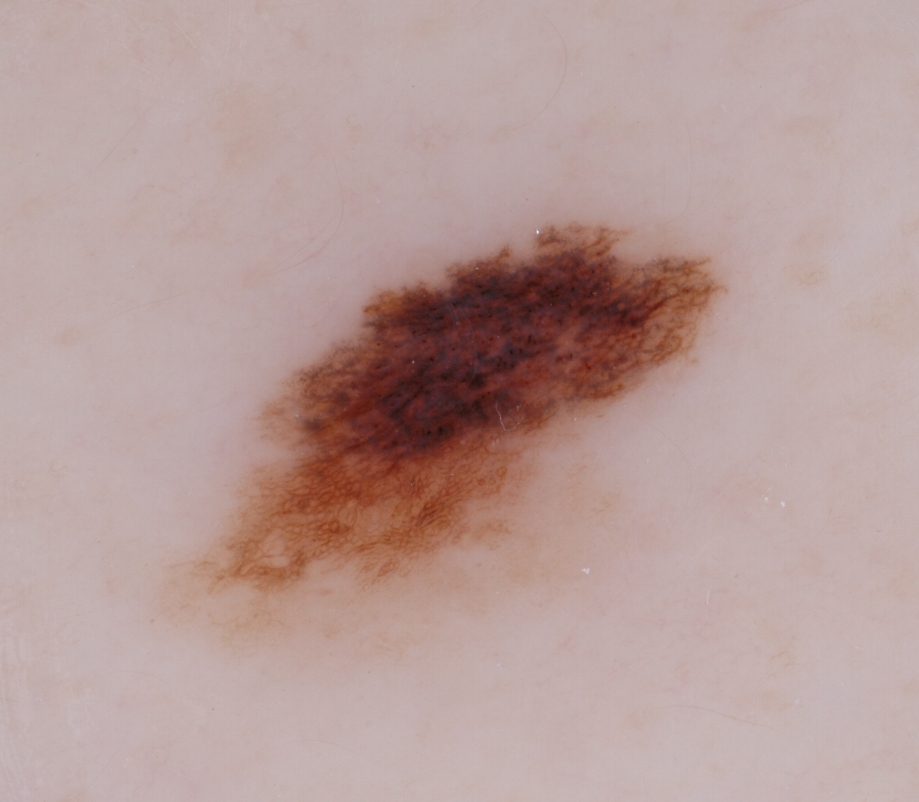A dermoscopic image of a skin lesion. The lesion is located at bbox(165, 193, 727, 652). Dermoscopic review identifies pigment network. Diagnosed as a melanocytic nevus, a benign lesion.